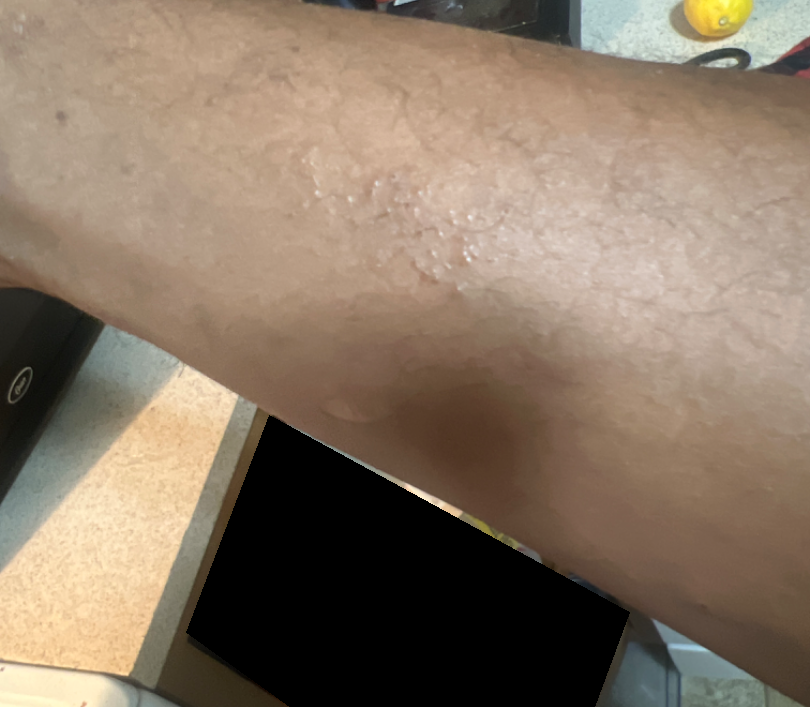Q: Patient demographics?
A: male, age 18–29
Q: Patient's own categorization?
A: a rash
Q: What symptoms does the patient report?
A: itching
Q: What is the framing?
A: close-up
Q: How long has this been present?
A: less than one week
Q: What is the differential diagnosis?
A: favoring Lichen spinulosus; also consider Lichen nitidus; possibly Eczema